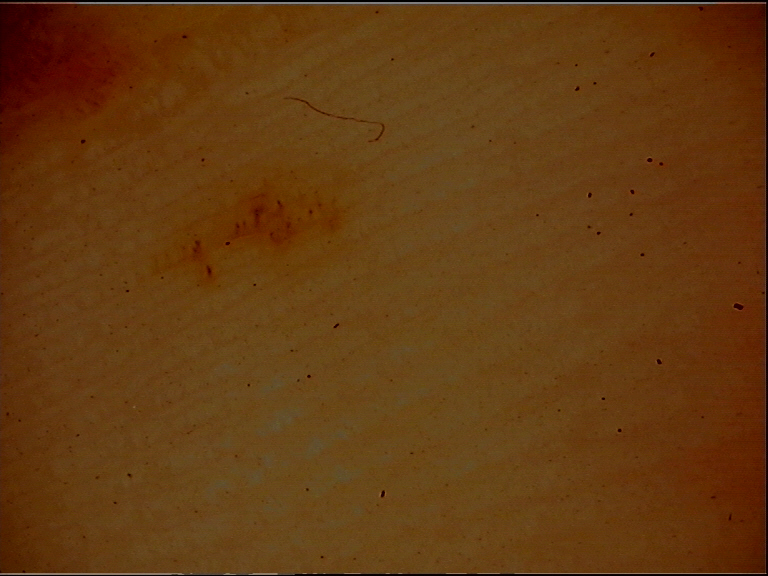Summary:
A dermoscopy image of a single skin lesion. The morphology is that of a banal lesion.
Conclusion:
Classified as an acral junctional nevus.